The lesion involves the leg · the photograph was taken at an angle — 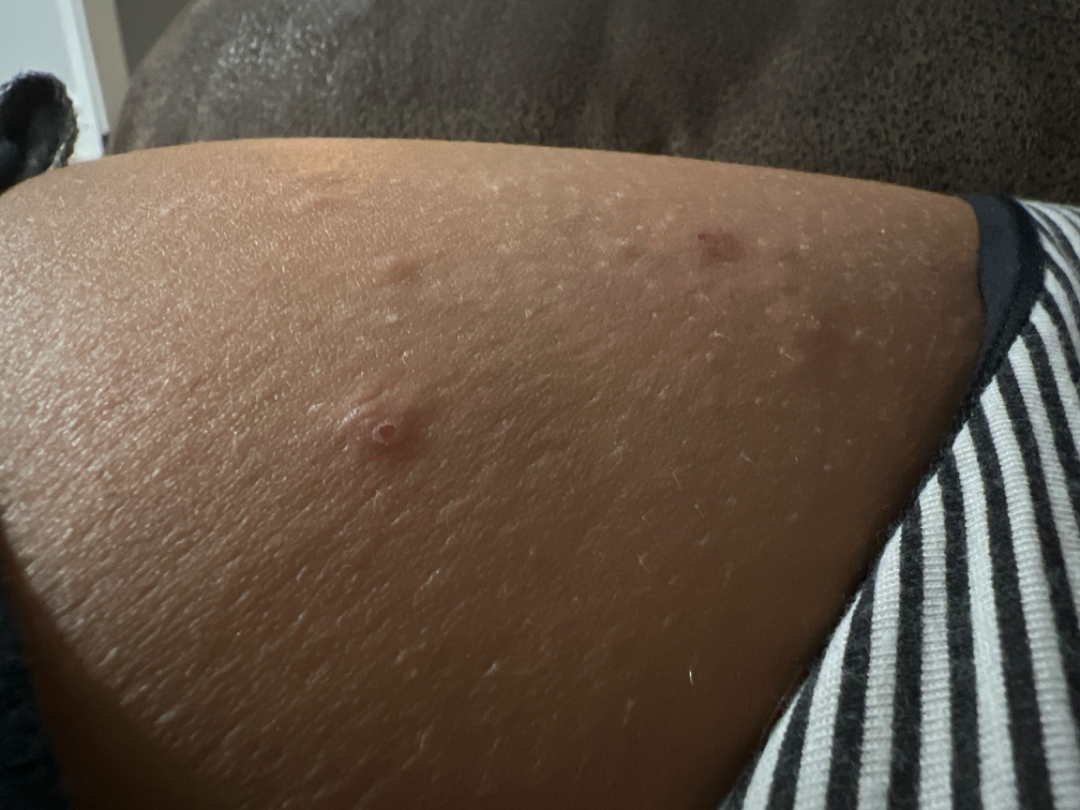Findings:
On remote dermatologist review: Impetigo, Insect Bite and Herpes Simplex were each considered, in no particular order.